A dermoscopic image of a skin lesion: 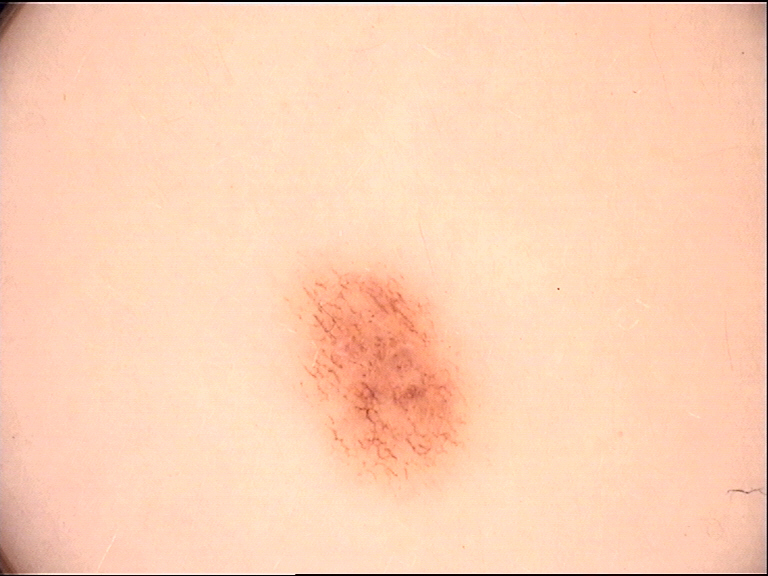diagnosis = dysplastic junctional nevus (expert consensus).